The contributor reports the lesion is raised or bumpy · no relevant systemic symptoms · the lesion is associated with itching and burning · the photograph was taken at an angle · reported duration is three to twelve months · the patient considered this a rash: 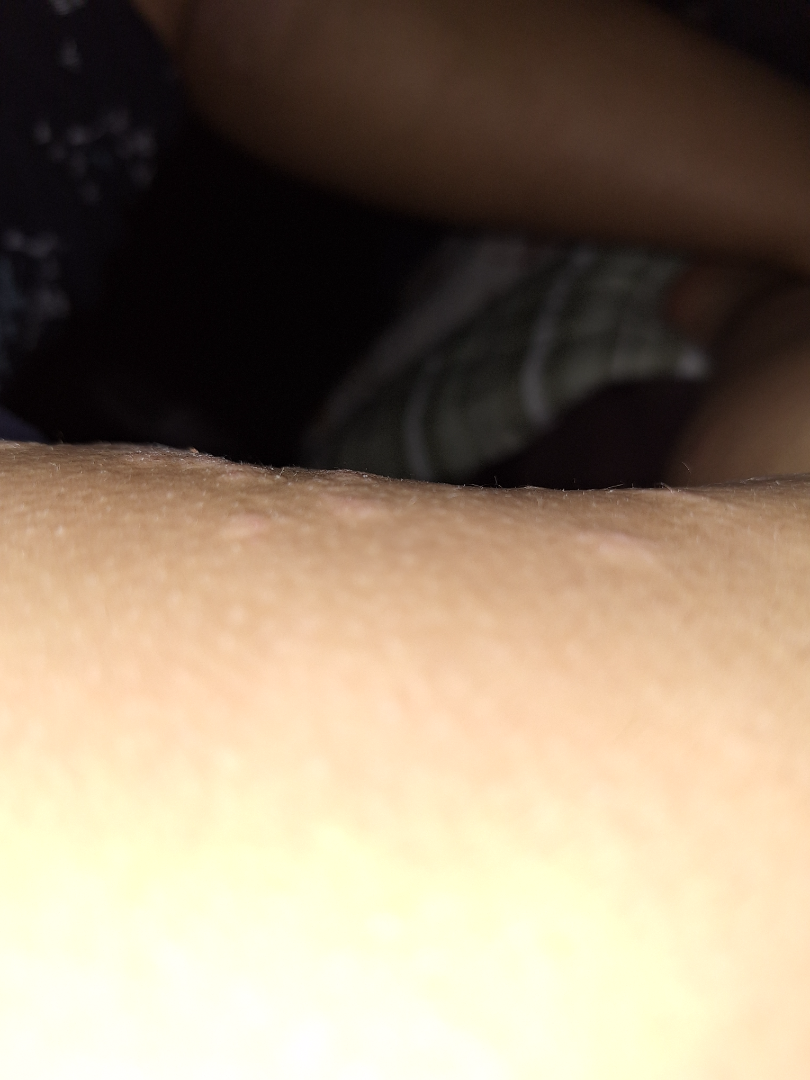differential = one reviewing dermatologist: the favored diagnosis is Urticaria; with consideration of Eczema.